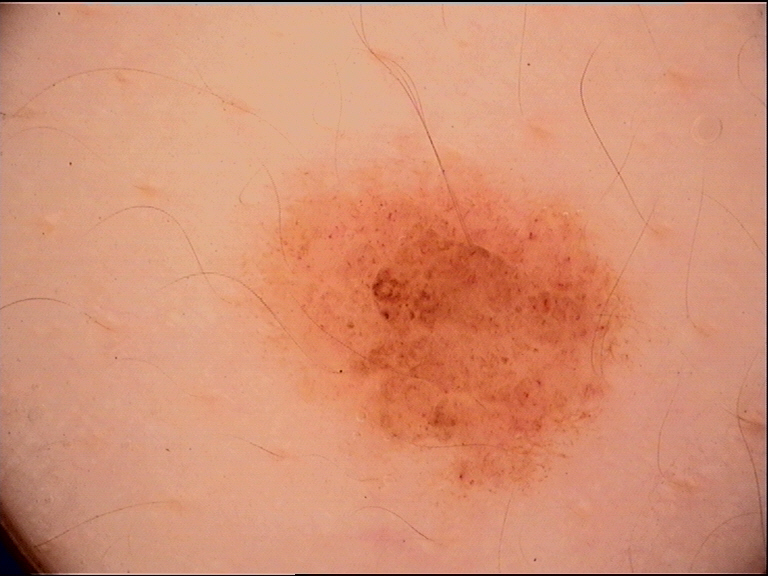Diagnosed as a compound nevus.